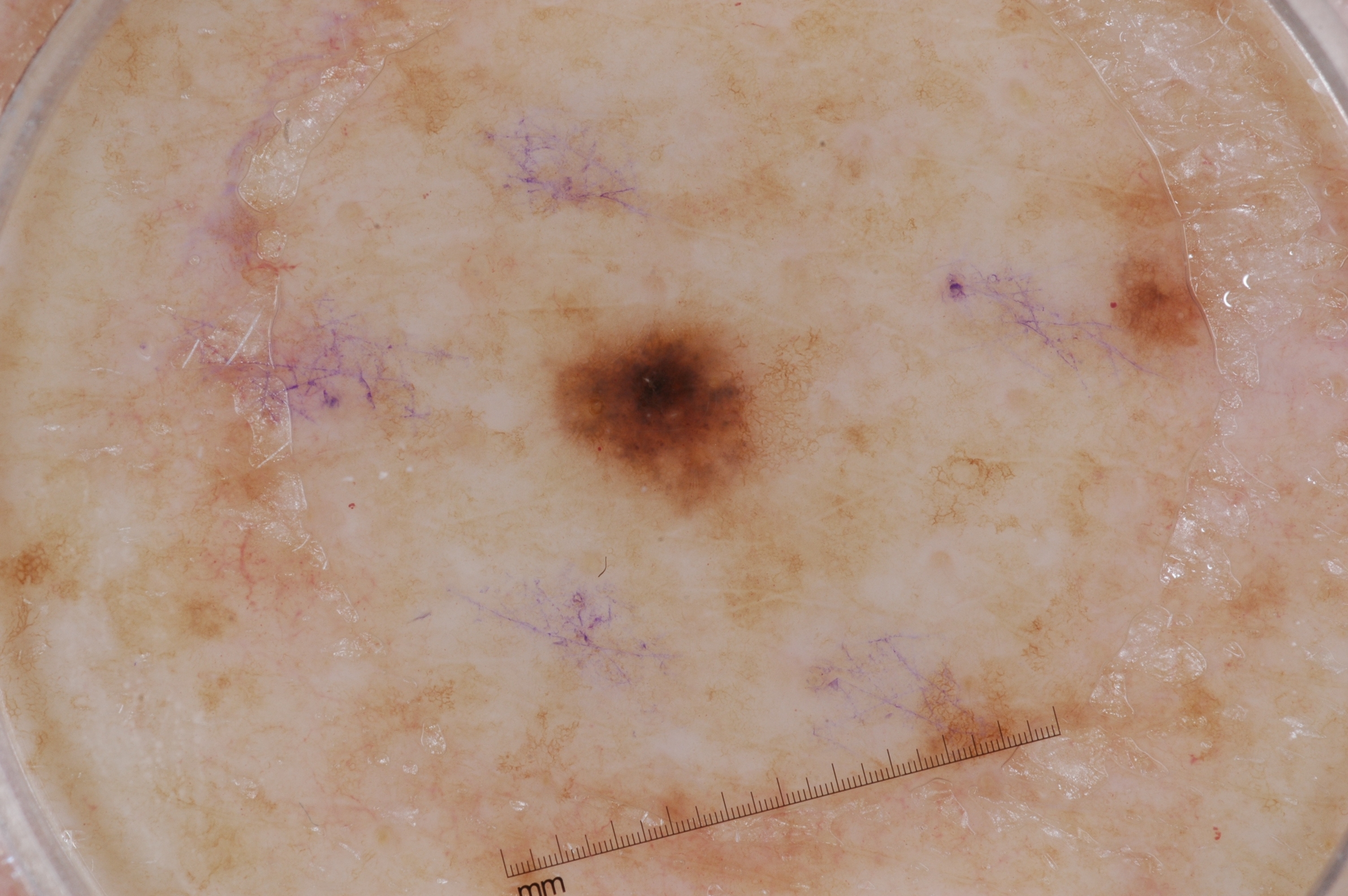Findings:
– imaging: dermoscopic image
– subject: female, about 75 years old
– dermoscopic findings: pigment network
– lesion location: x1=539 y1=288 x2=849 y2=542
– diagnostic label: a melanocytic nevus